The patient describes having few moles overall; a macroscopic clinical photograph of a skin lesion; the patient reports a personal history of skin cancer and a personal history of cancer; a male patient aged 76; referred for assessment of suspected basal cell carcinoma: 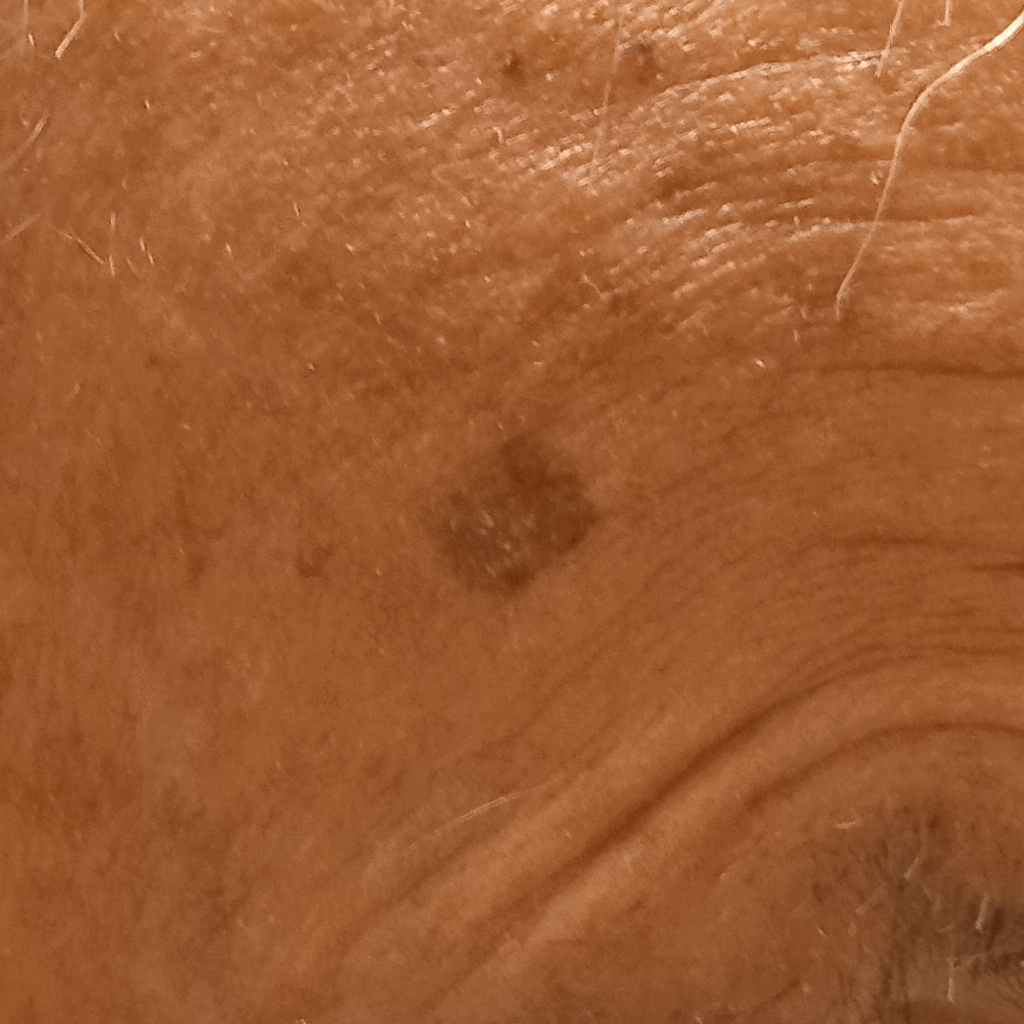Findings: The lesion involves the face. The lesion measures approximately 8.7 mm. Pathology: On biopsy, the diagnosis was a basal cell carcinoma, following excision, with tumor thickness 2.5 mm.